A dermoscopy image of a single skin lesion: 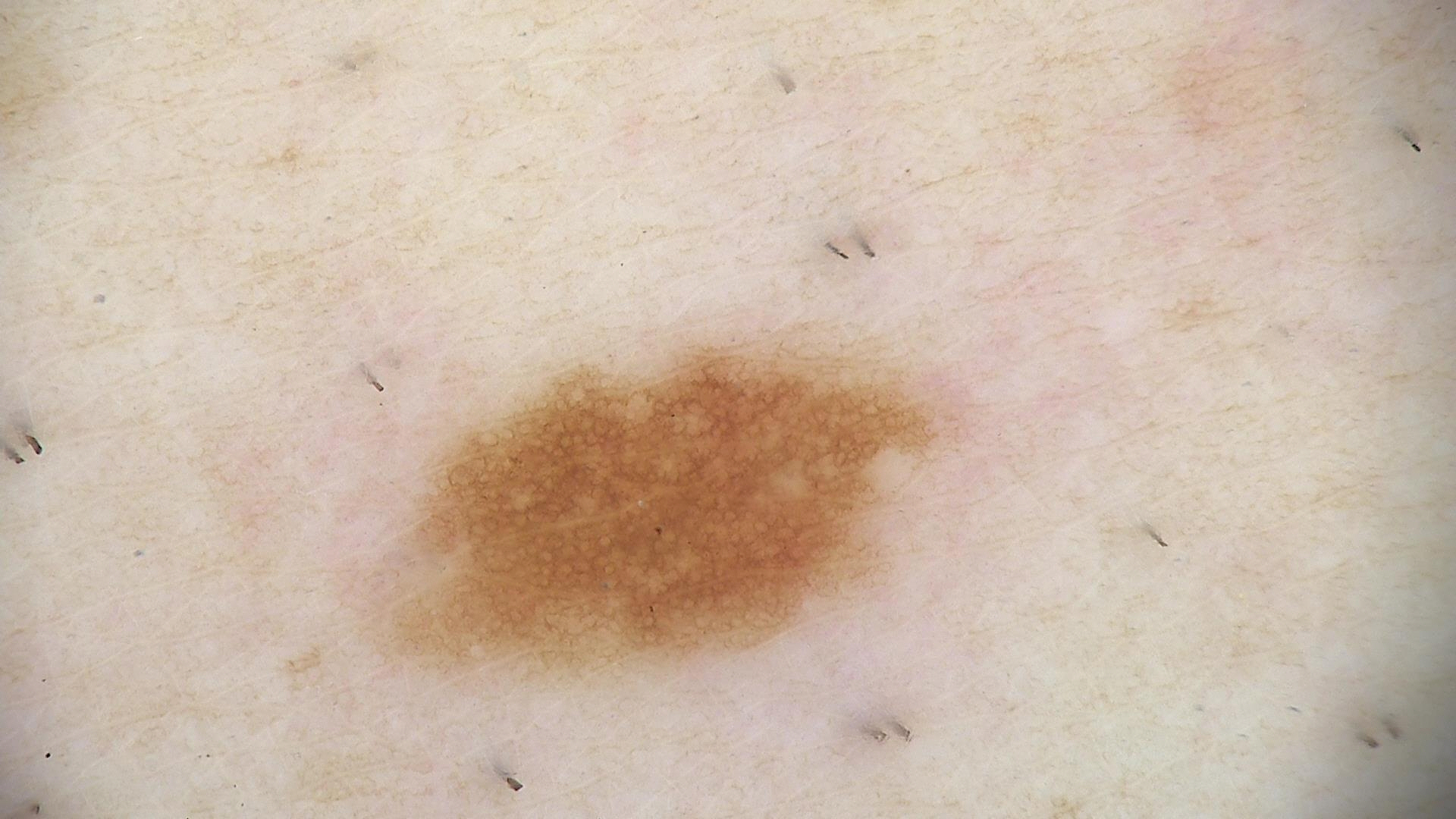The diagnosis was a dysplastic junctional nevus.